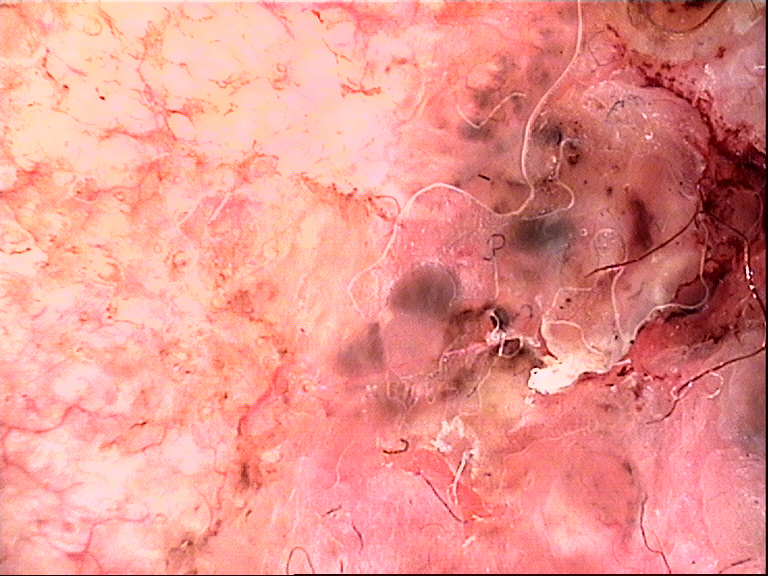This is a keratinocytic lesion.
Histopathology confirmed a malignant lesion — a basal cell carcinoma.